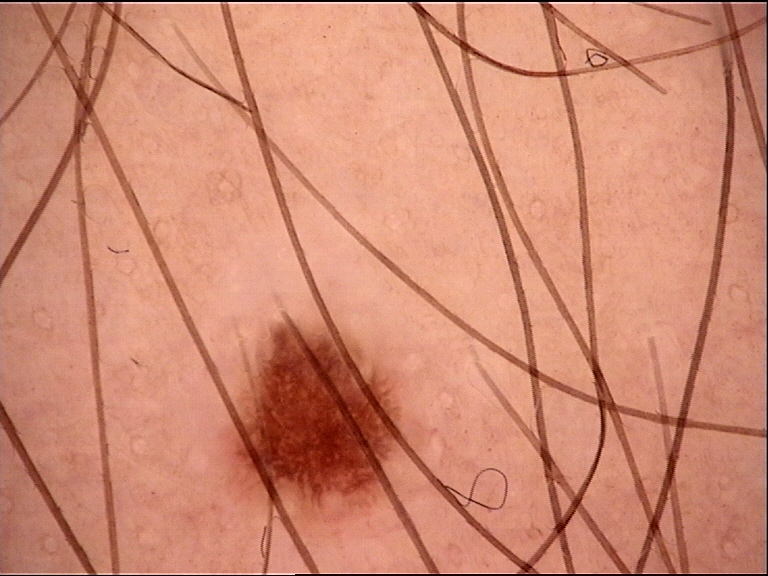{
  "image": "dermoscopy",
  "diagnosis": {
    "name": "dysplastic junctional nevus",
    "code": "jd",
    "malignancy": "benign",
    "super_class": "melanocytic",
    "confirmation": "expert consensus"
  }
}